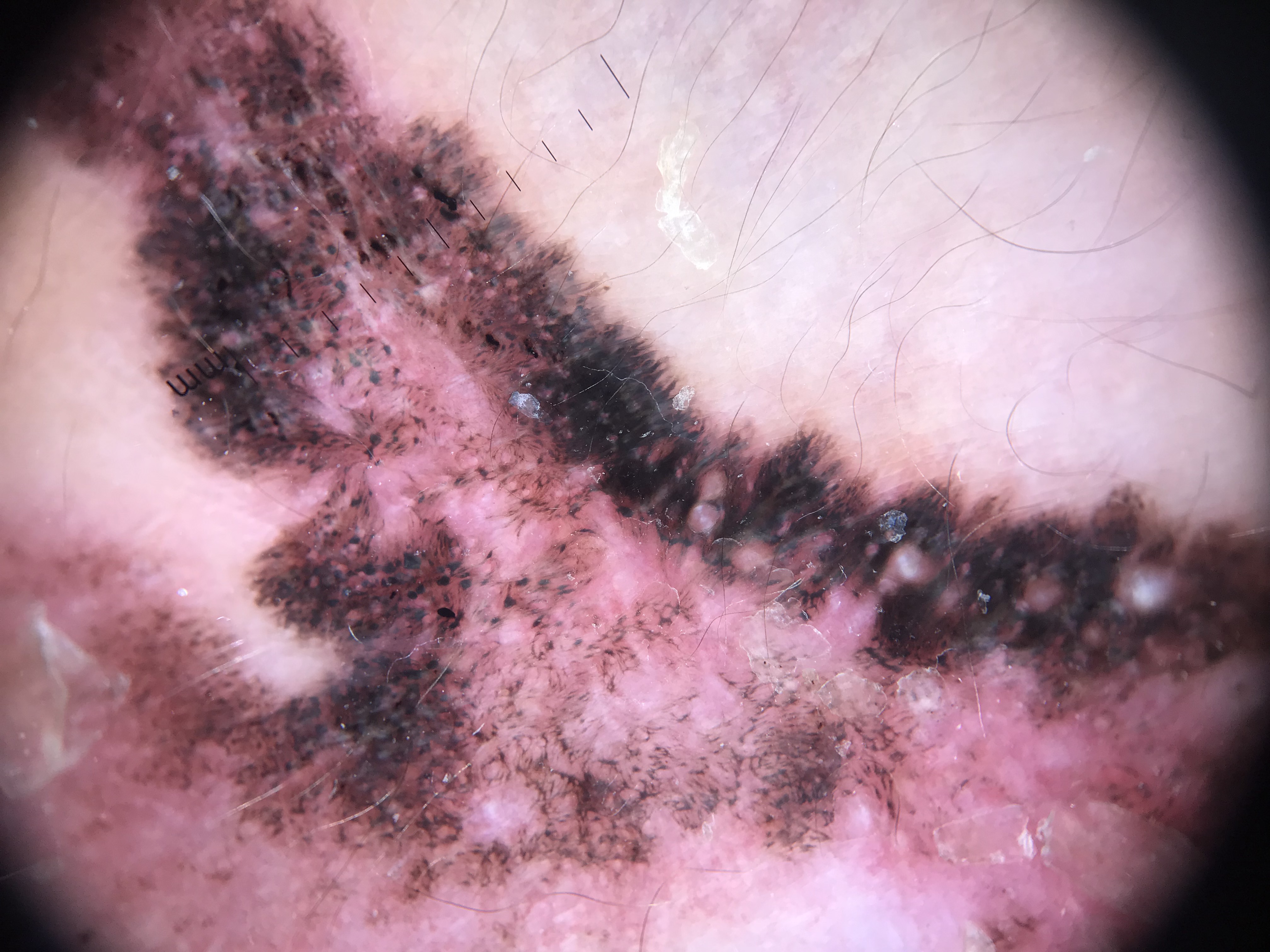Conclusion: Histopathologically confirmed as a melanoma.